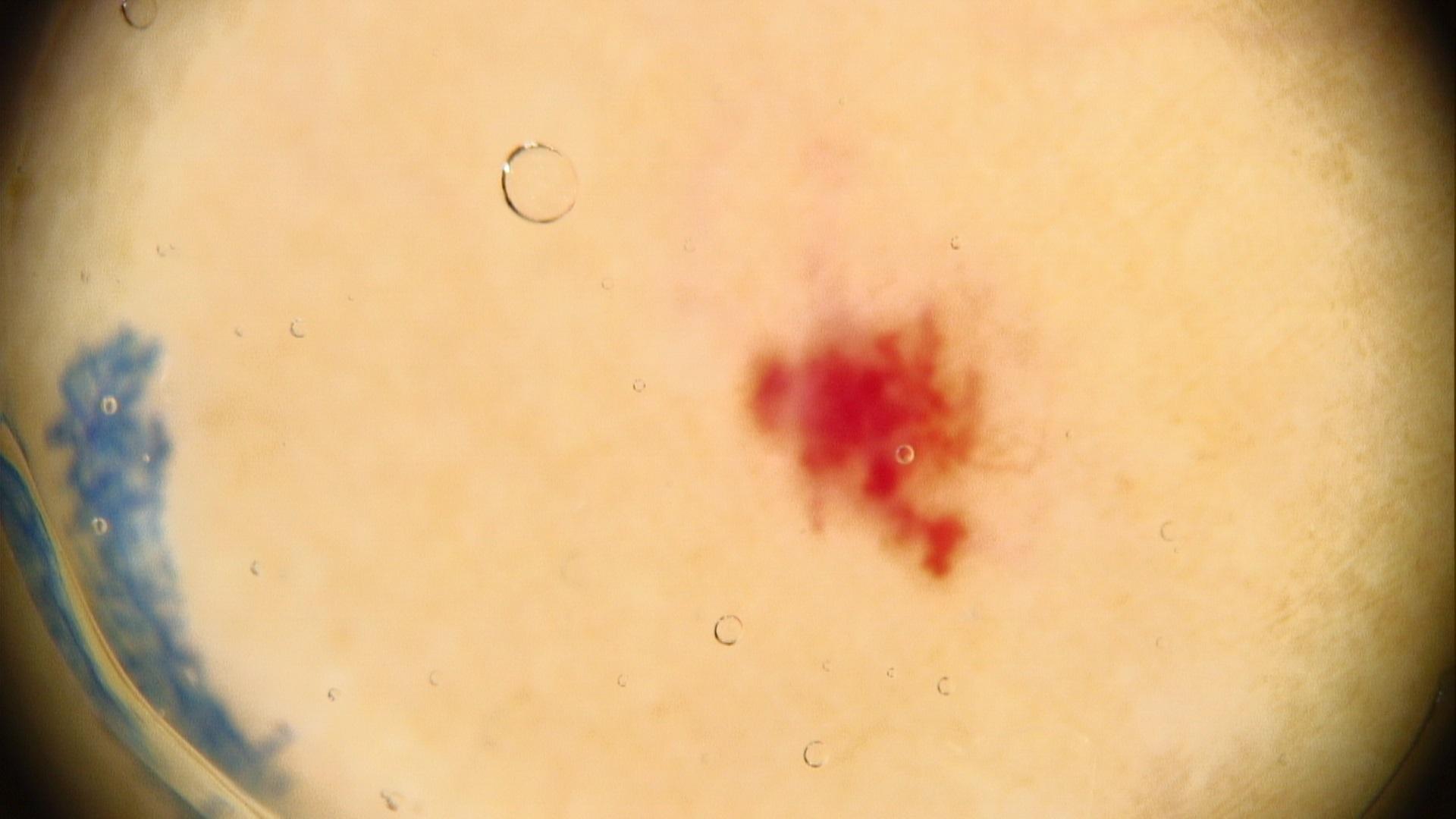{
  "patient": {
    "age_approx": 50,
    "sex": "male"
  },
  "skin_type": "III",
  "image": "dermoscopy",
  "lesion_location": {
    "region": "a lower extremity"
  },
  "diagnosis": {
    "name": "vascular lesion",
    "malignancy": "benign",
    "confirmation": "expert clinical impression"
  }
}